A skin lesion imaged with a dermatoscope:
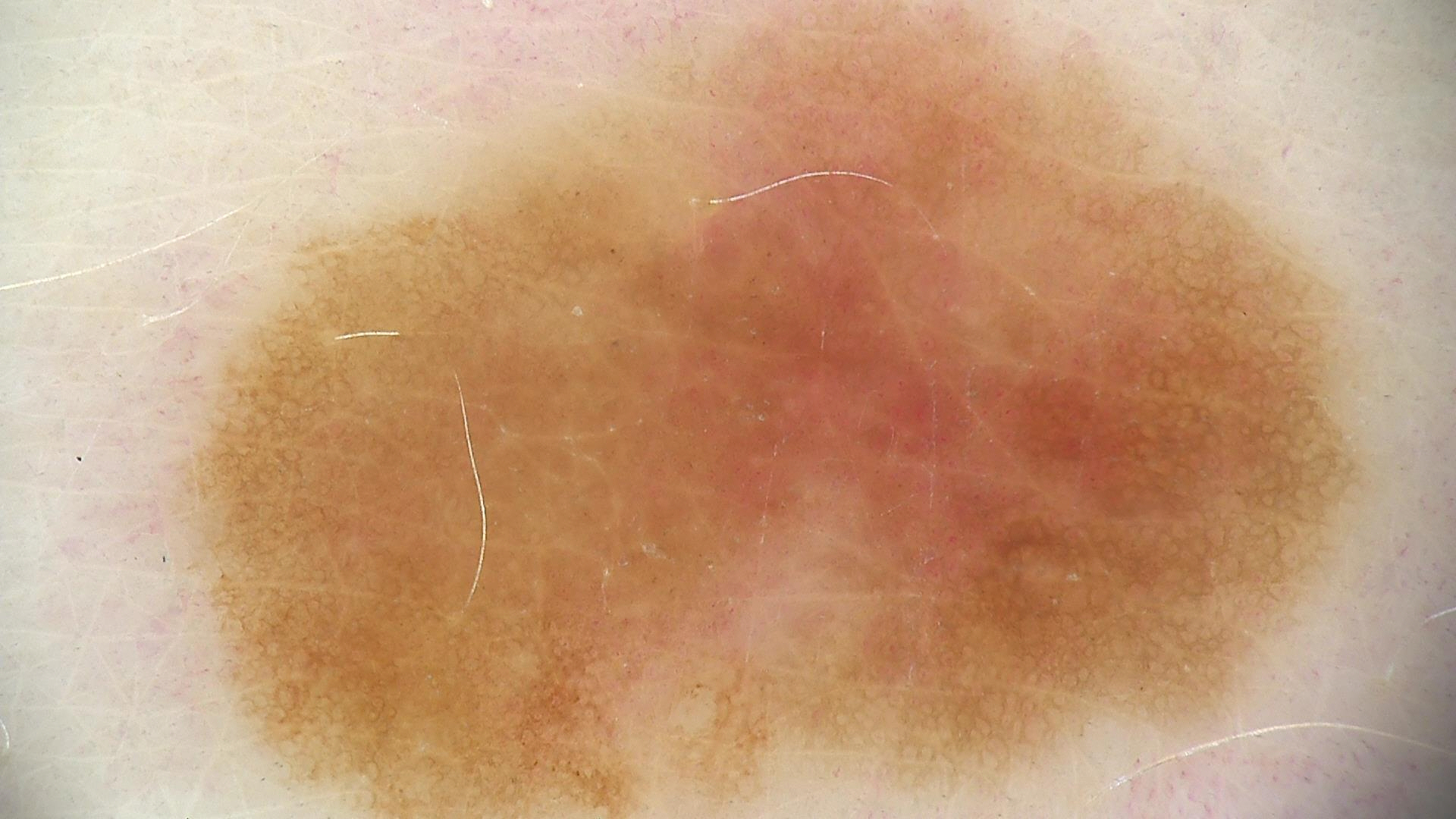class = dysplastic junctional nevus (expert consensus).